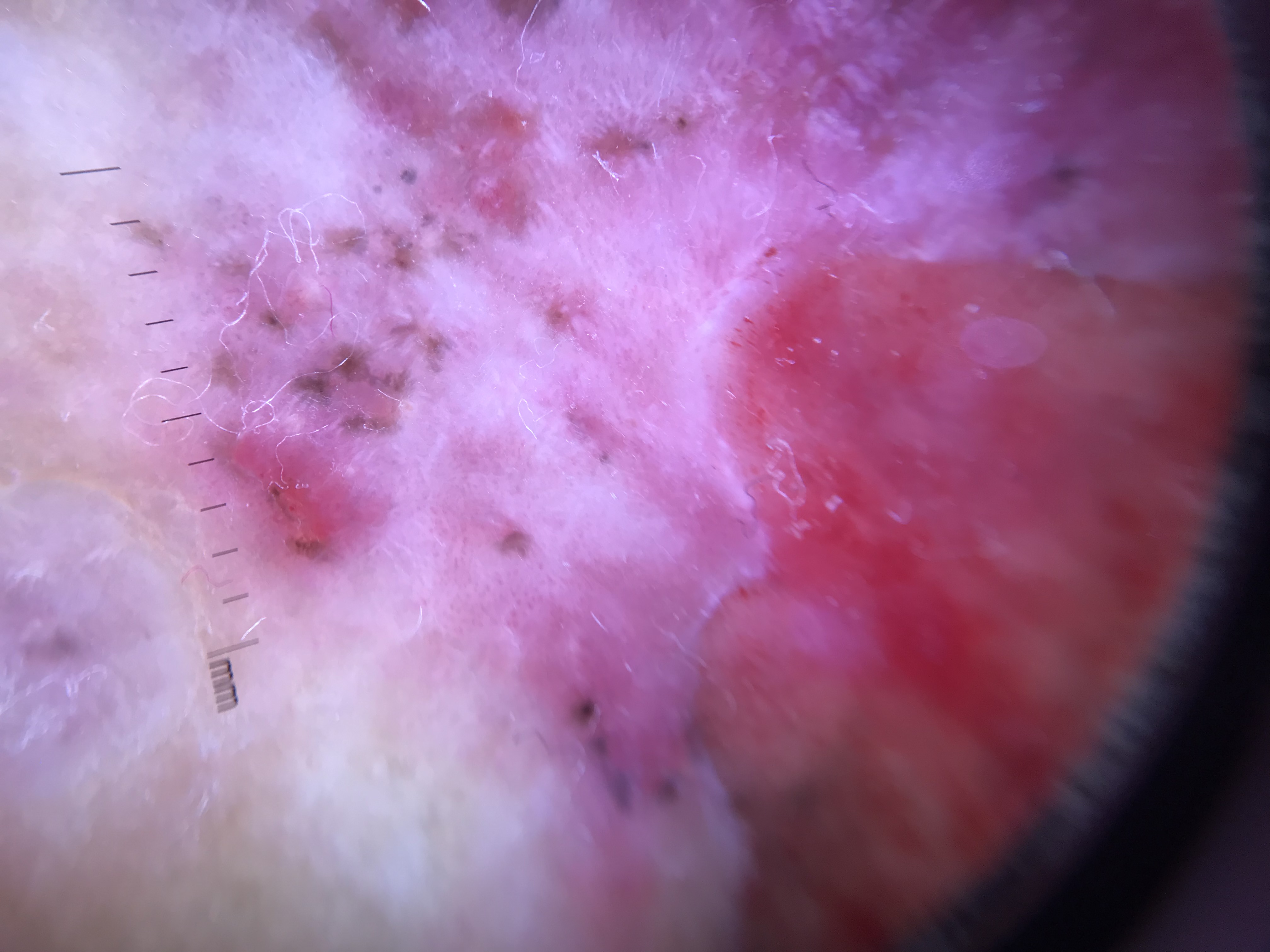Q: What is the imaging modality?
A: dermatoscopy
Q: What is this lesion?
A: basal cell carcinoma (biopsy-proven)